A dermatoscopic image of a skin lesion:
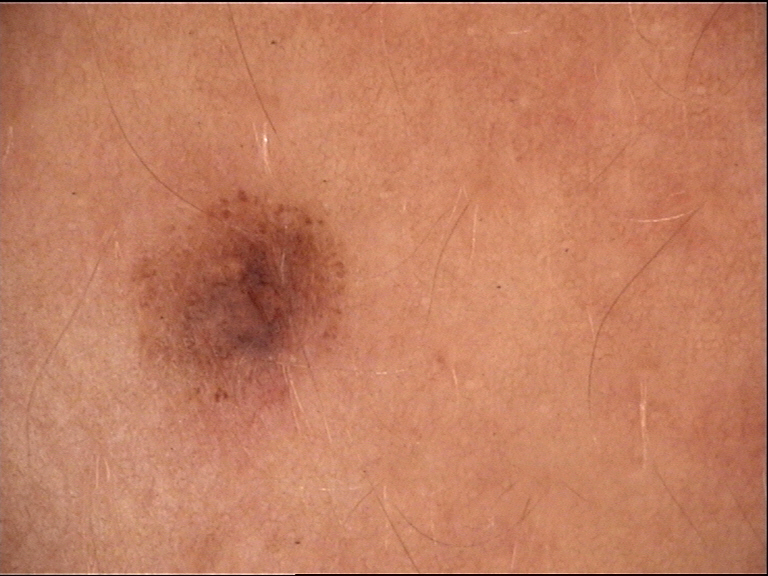The diagnosis was a benign lesion — a dysplastic junctional nevus.